The contributor is female; the affected area is the leg, arm and head or neck; a close-up photograph.
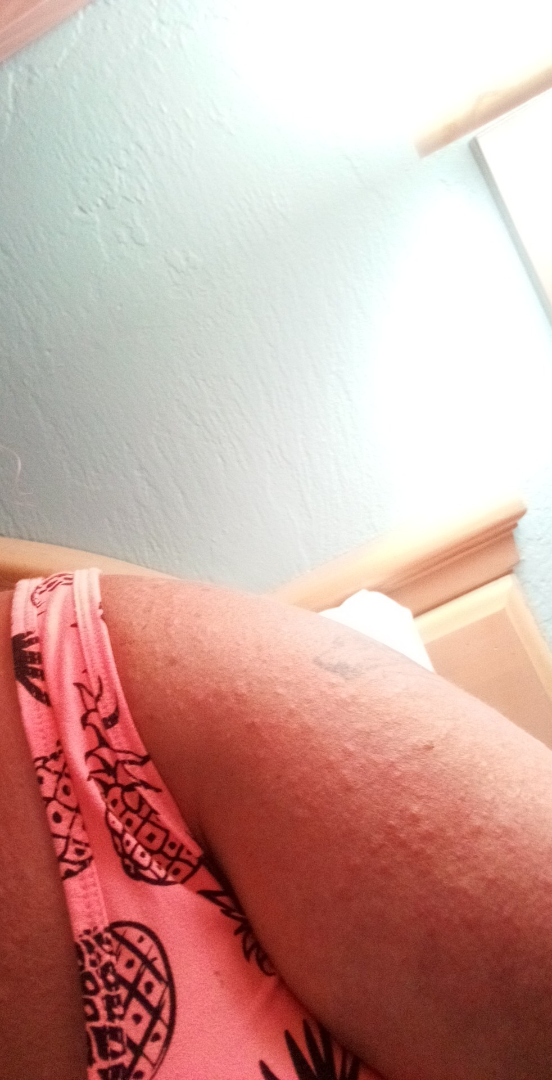assessment: not assessable
systemic_symptoms: chills
patient_category: a rash
symptoms:
  - itching
  - pain
  - burning